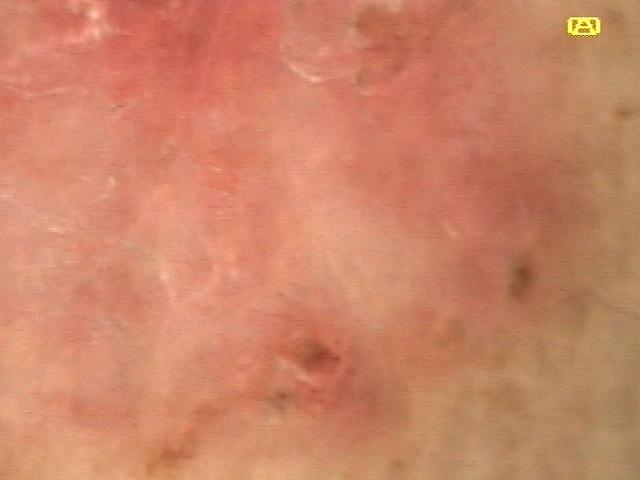| key | value |
|---|---|
| image type | contact-polarized dermoscopy |
| FST | II |
| relevant background | a previous melanoma |
| patient | female, aged 53-57 |
| anatomic site | the posterior trunk |
| diagnosis | Basal cell carcinoma (biopsy-proven) |